A dermoscopic image of a skin lesion, the patient is a male in their mid- to late 40s:
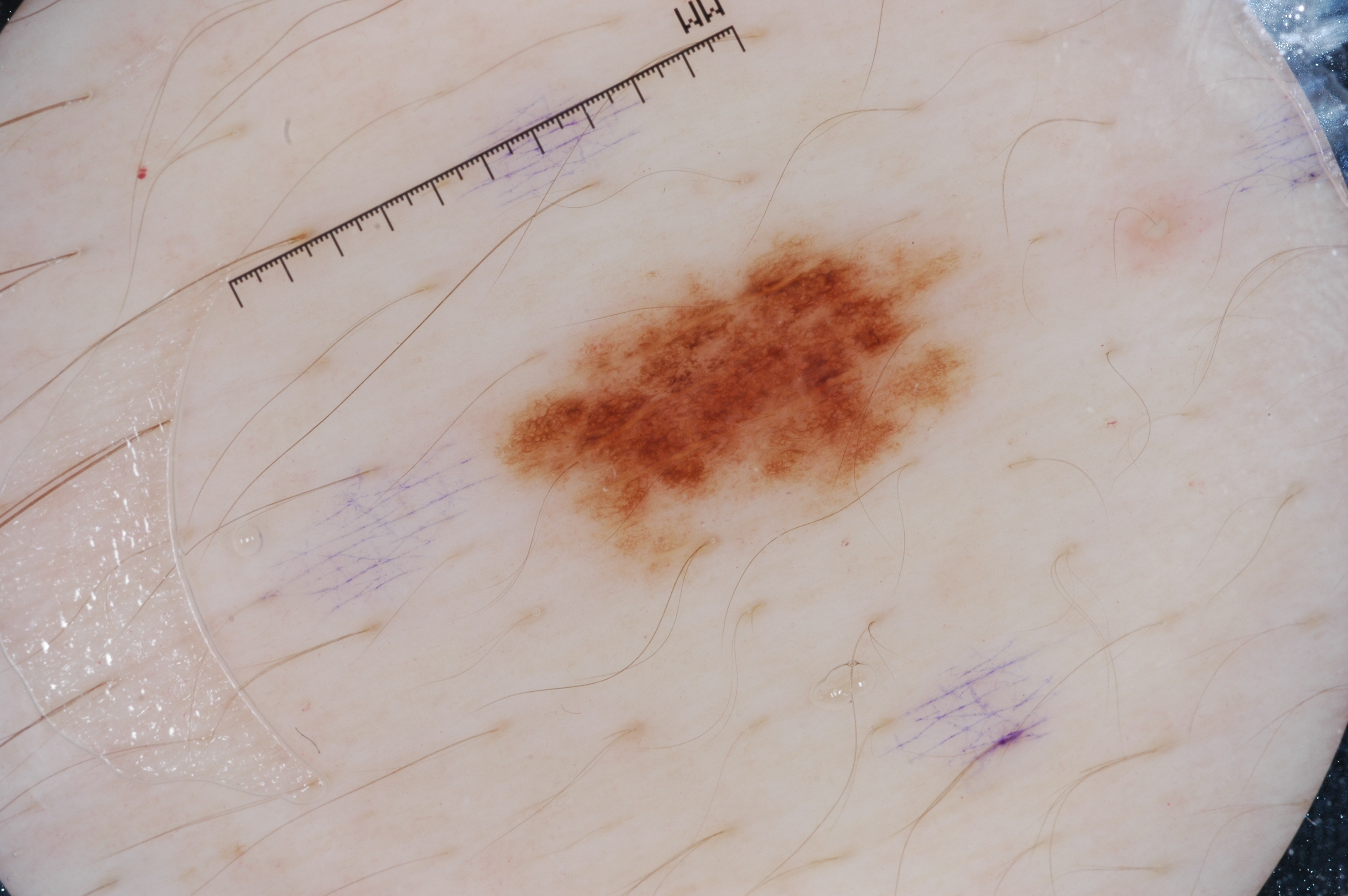The visible lesion spans x1=473, y1=205, x2=1010, y2=593.
Dermoscopic examination shows pigment network; no milia-like cysts, negative network, or streaks.
The lesion was assessed as a melanocytic nevus.